Symptoms reported: itching · present for less than one week · the contributor notes the lesion is fluid-filled · the patient described the issue as a rash · this image was taken at an angle · the leg and top or side of the foot are involved · the patient is a male aged 30–39:
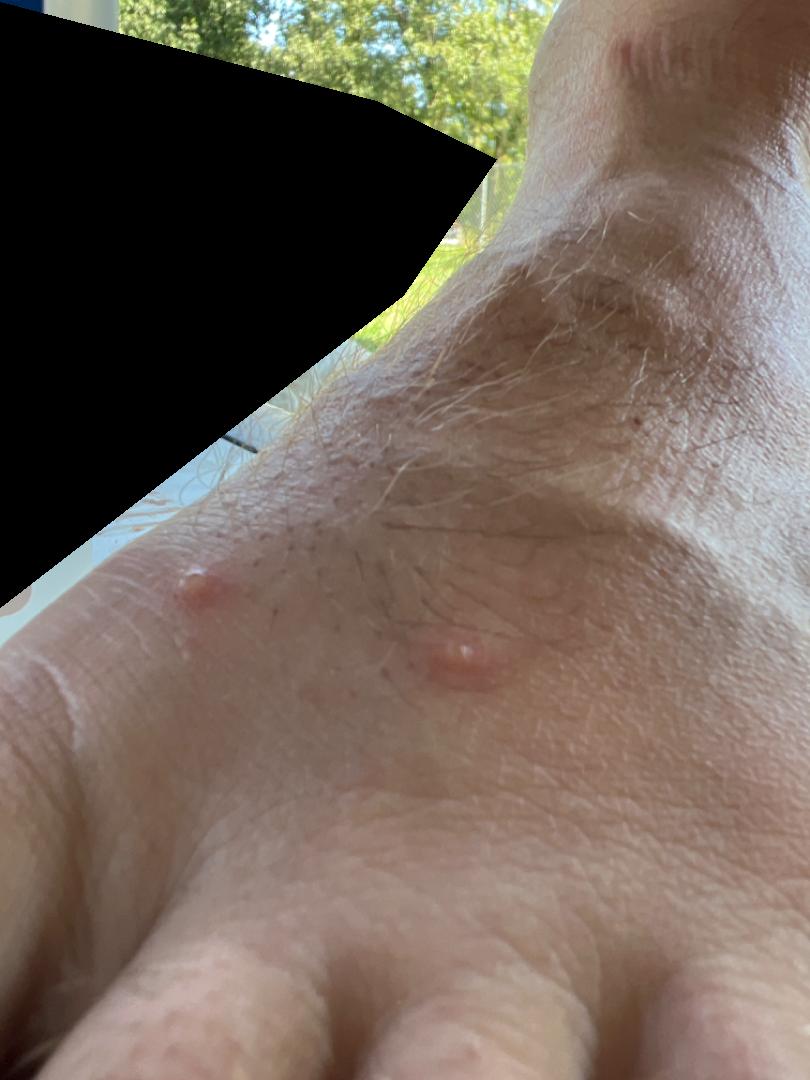• dermatologist impression: Insect Bite (possible); Molluscum Contagiosum (possible)